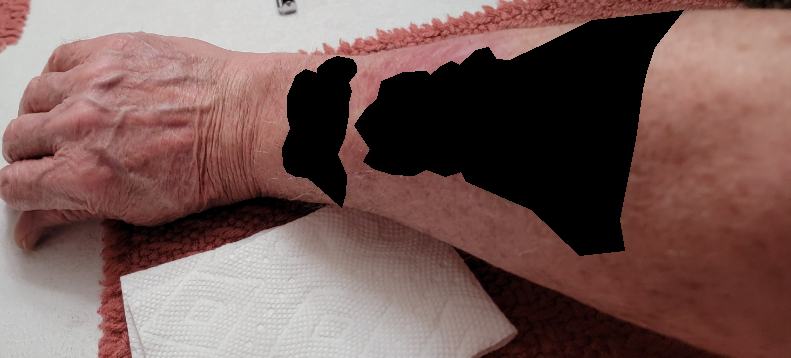Consistent with Eczema.